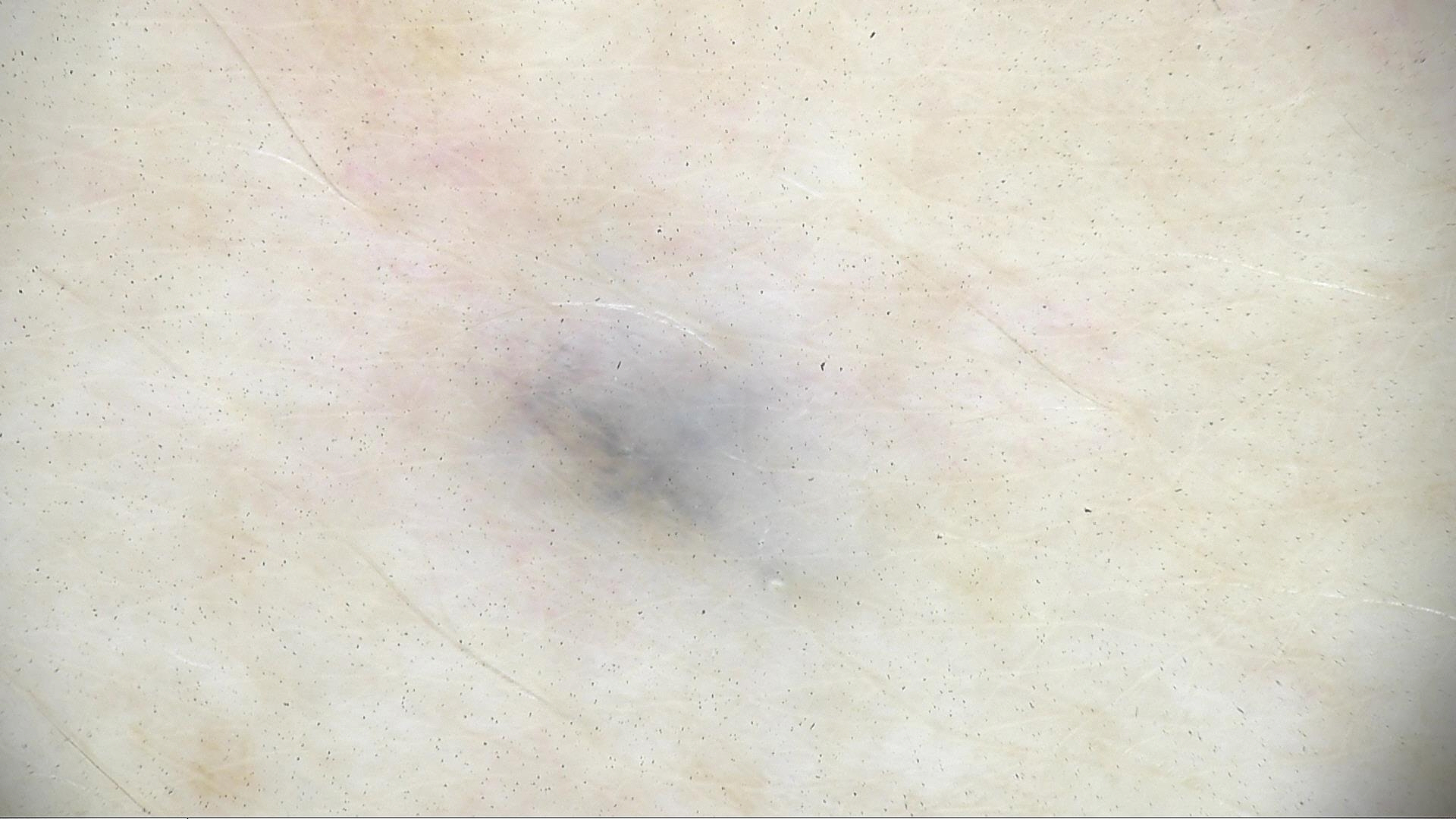Q: What kind of image is this?
A: dermatoscopy
Q: What is the lesion category?
A: dermal, banal
Q: What is the diagnosis?
A: blue nevus (expert consensus)